The photograph is a close-up of the affected area: 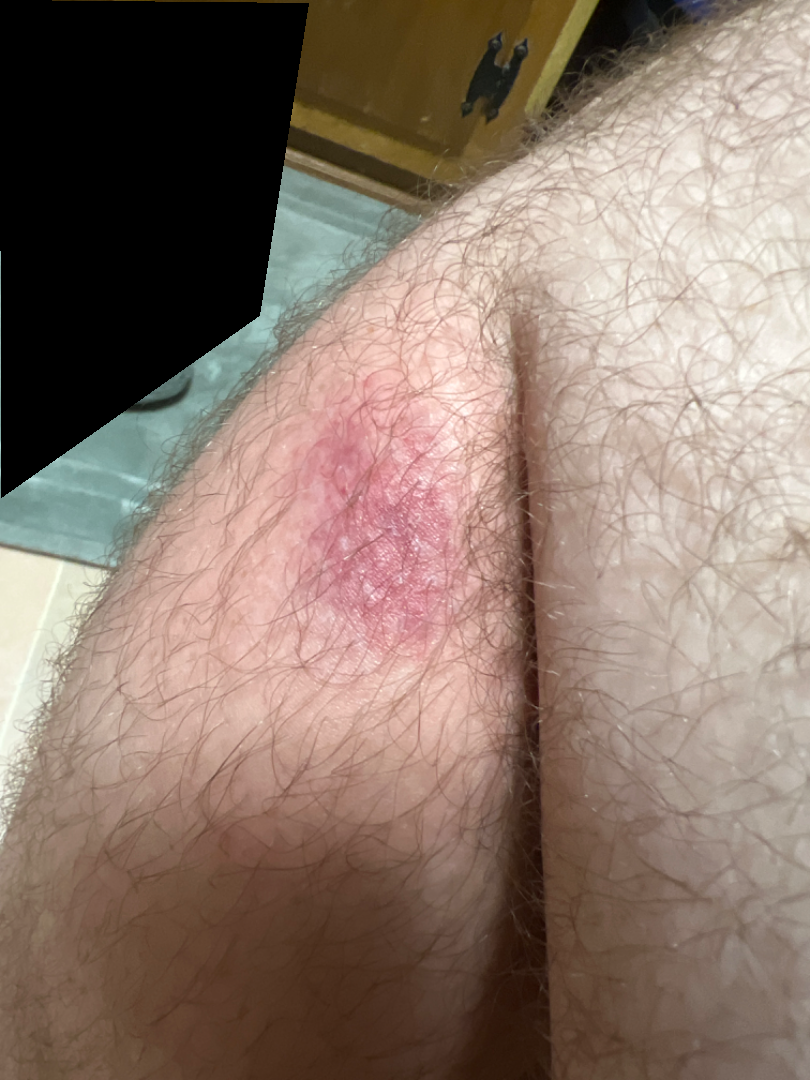History: Texture is reported as fluid-filled and raised or bumpy. FST III; lay reviewers estimated a MST of 2. Impression: On remote dermatologist review, favoring Eczema; the differential also includes Psoriasis; a more distant consideration is Allergic Contact Dermatitis.